A dermatoscopic image of a skin lesion.
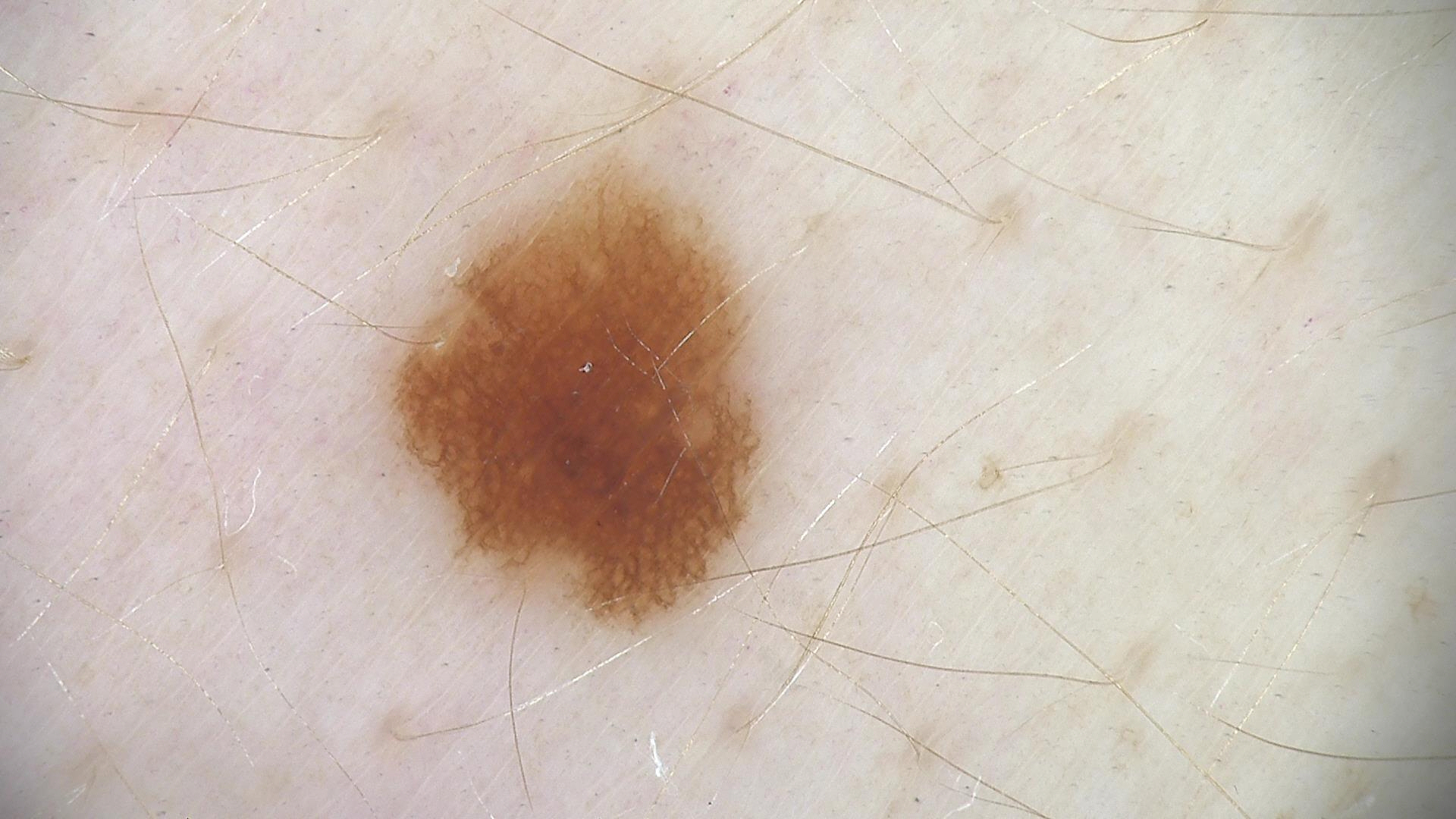The diagnostic label was a benign lesion — a dysplastic junctional nevus.